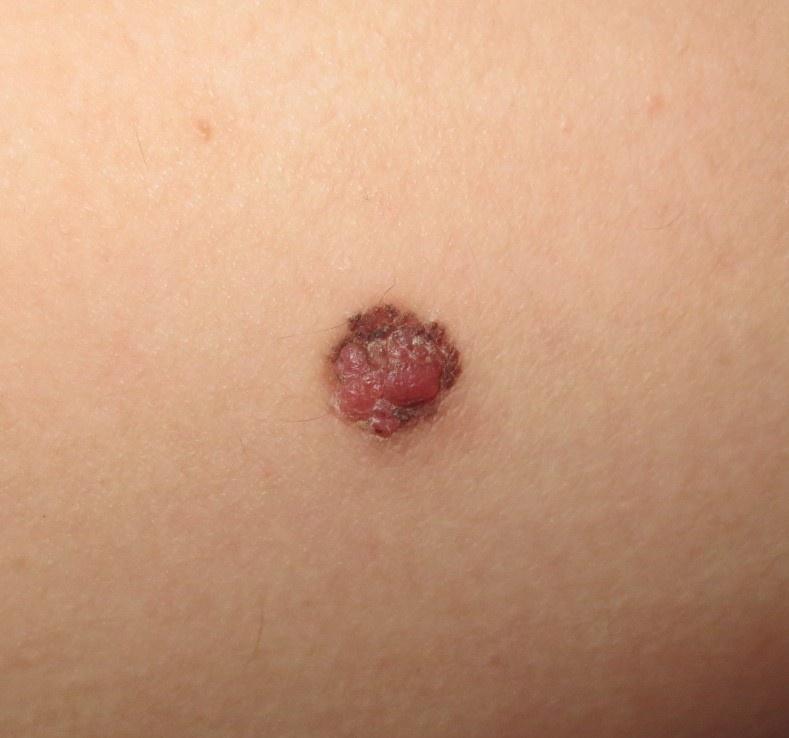Histopathology confirmed a melanoma.